By self-report, a personal history of skin cancer, a personal history of cancer, no sunbed use, and no immunosuppression; the patient says their skin tans without first burning; a dermoscopy image of a skin lesion; few moles overall by the patient's own estimate; a female patient 60 years of age; referred for assessment of suspected basal cell carcinoma — 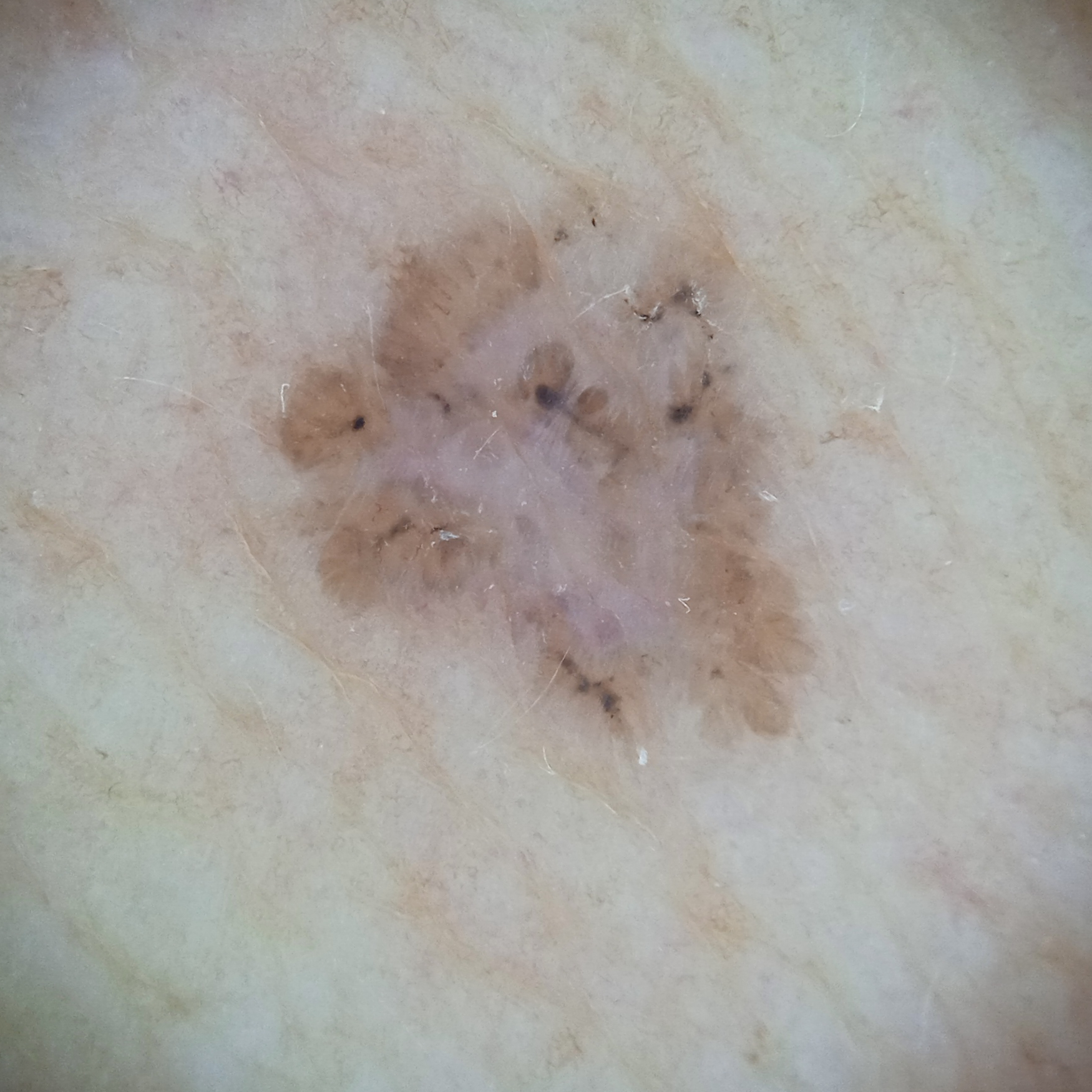Summary: Located on the torso. Measuring roughly 7.2 mm. Impression: The lesion was assessed as a basal cell carcinoma.